A dermatoscopic image of a skin lesion: 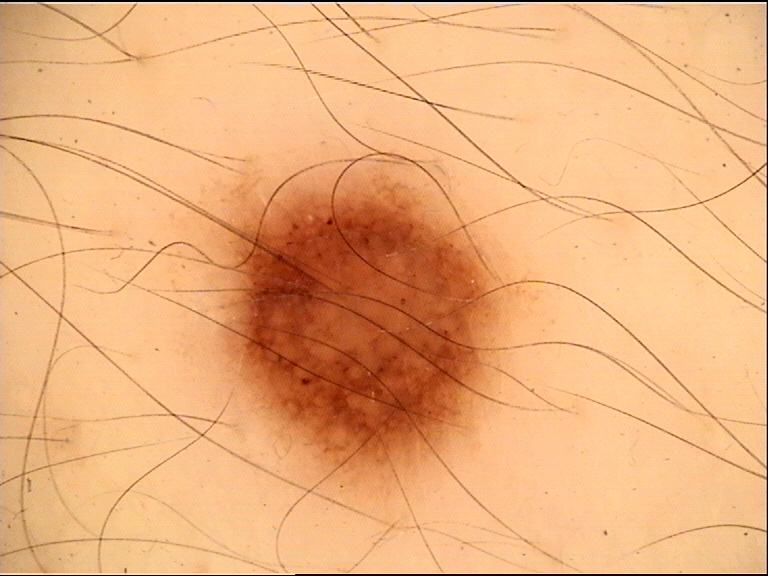Conclusion:
Classified as a benign lesion — a dysplastic junctional nevus.